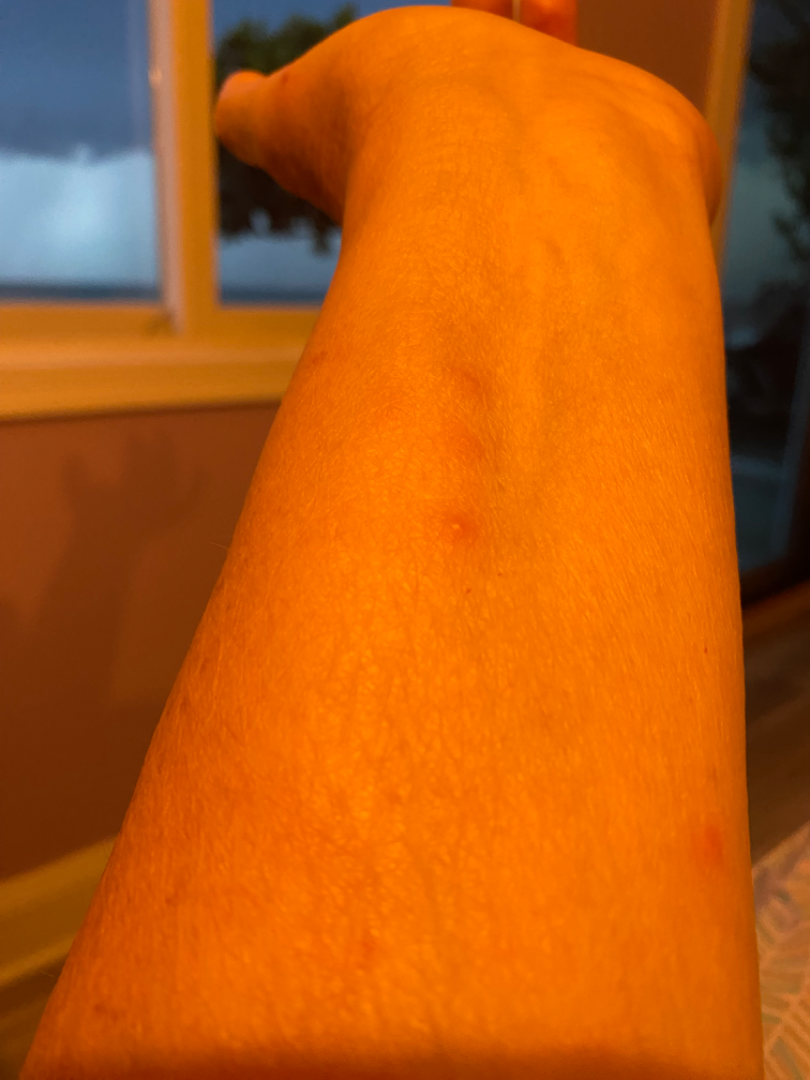impression — reviewed remotely by one dermatologist: the favored diagnosis is Insect Bite; with consideration of Urticaria; the differential also includes Allergic Contact Dermatitis.